Texture is reported as raised or bumpy · skin tone: FST III; lay reviewers estimated Monk skin tone scale 3 (US pool) or 2 (India pool) · the condition has been present for about one day · the photograph was taken at a distance · the affected area is the leg — 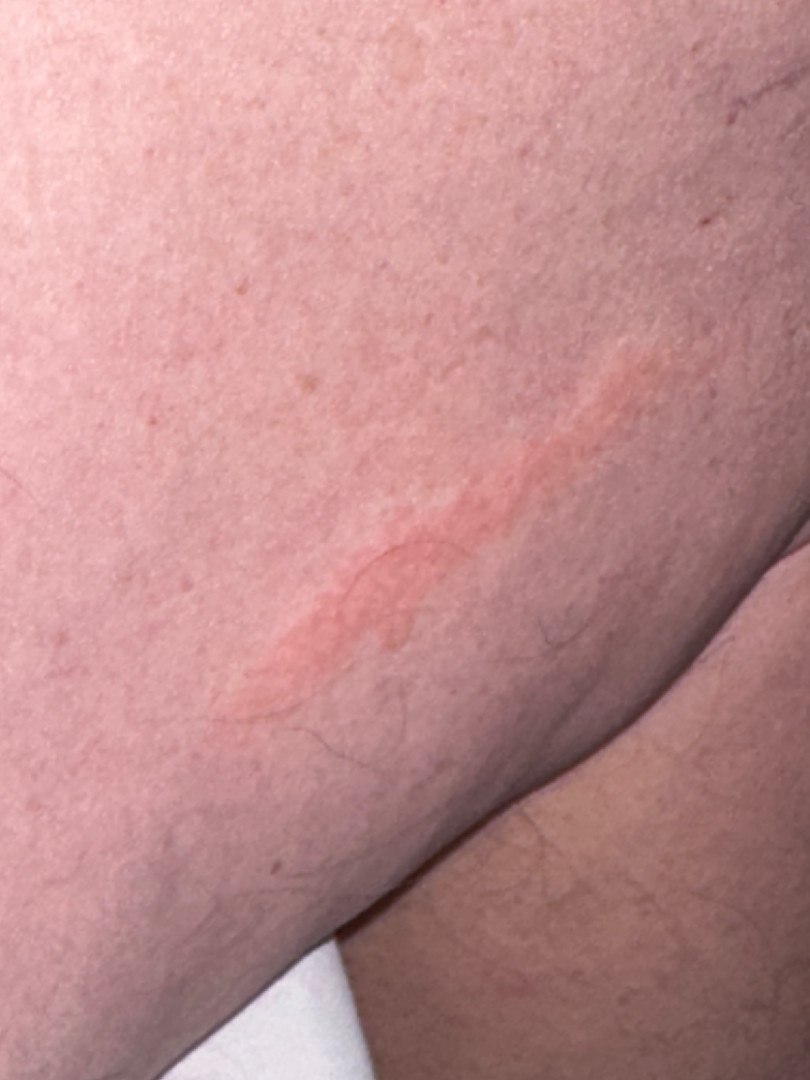Q: What conditions are considered?
A: the differential is split between Urticaria and Allergic Contact Dermatitis